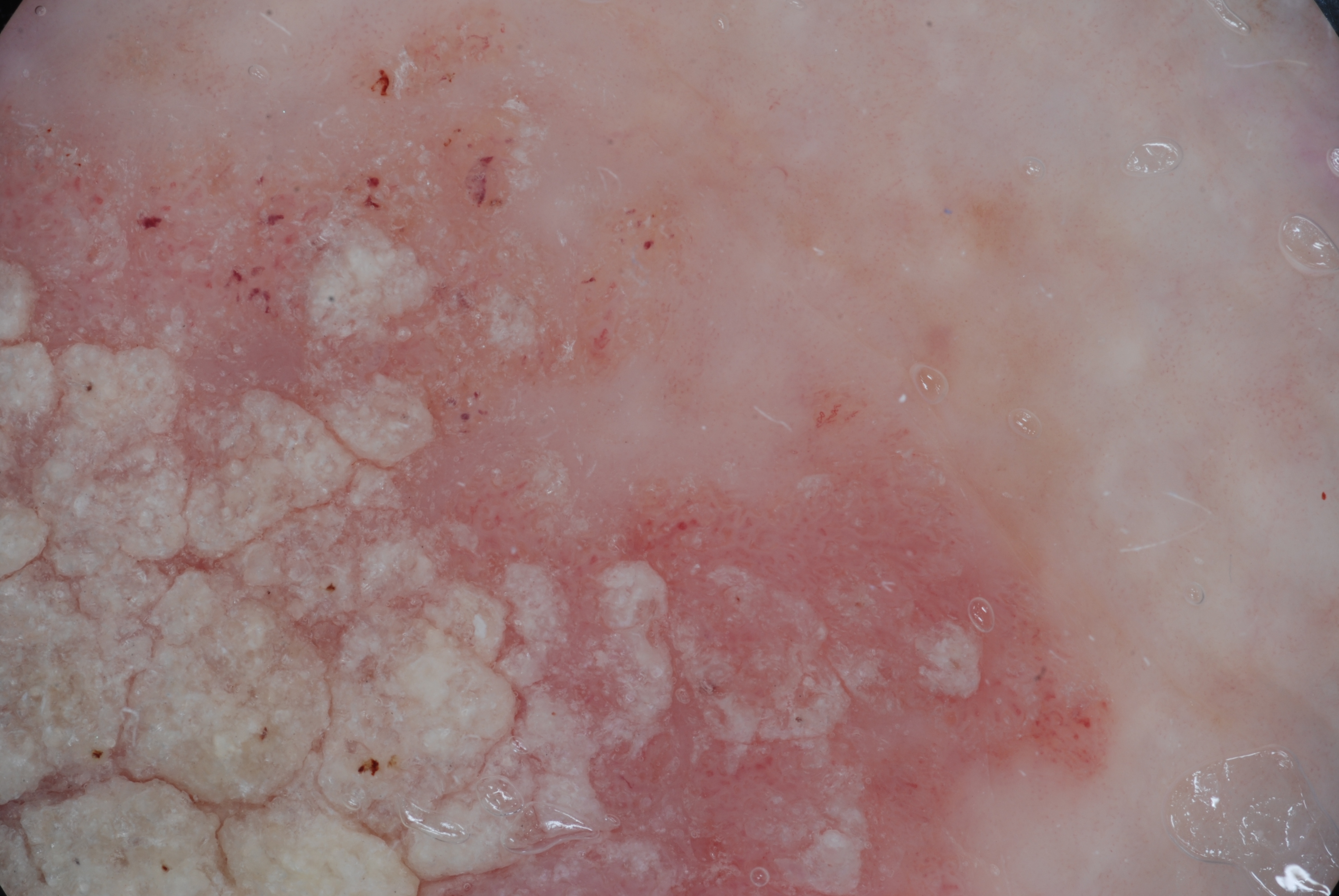image:
  modality: dermoscopy
lesion_location:
  bbox_xyxy:
    - 1
    - 2
    - 1131
    - 895
dermoscopic_features:
  present: []
  absent:
    - streaks
    - negative network
    - pigment network
    - milia-like cysts
diagnosis:
  name: seborrheic keratosis
  malignancy: benign
  lineage: keratinocytic
  provenance: clinical